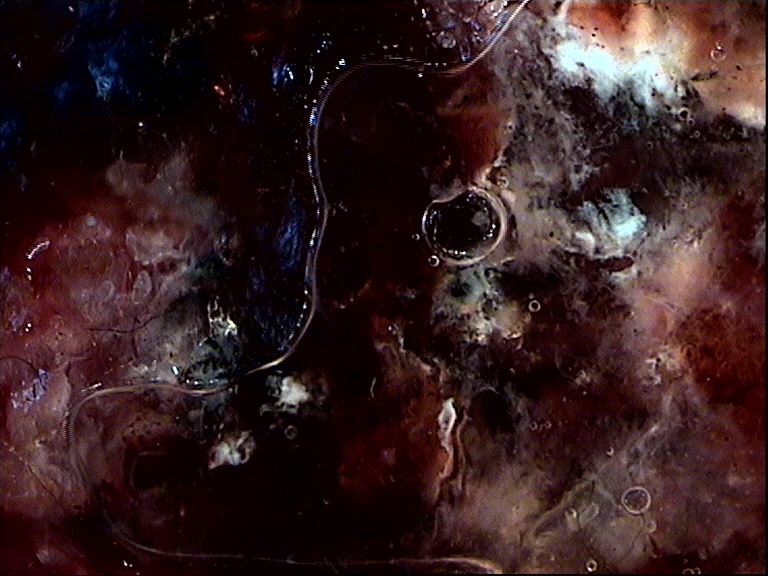Findings:
A dermoscopy image of a single skin lesion.
Diagnosis:
Confirmed on histopathology as a melanoma.